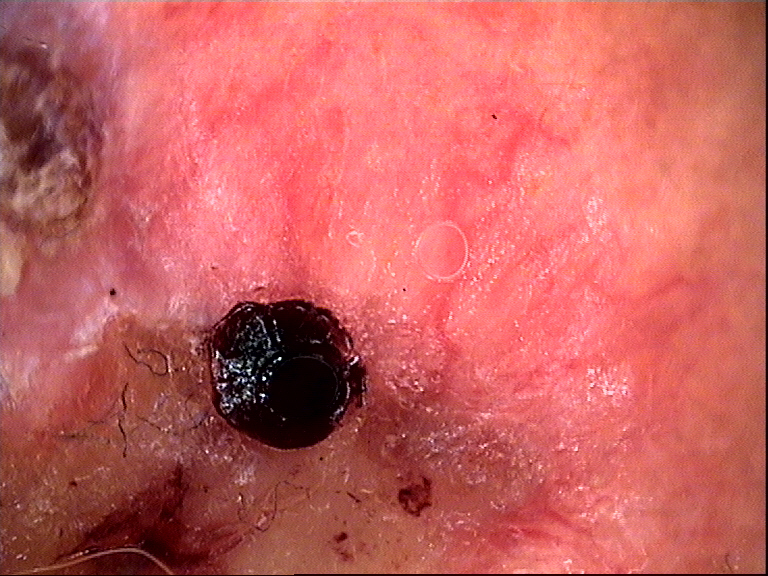Q: How is the lesion classified?
A: keratinocytic
Q: What is this lesion?
A: squamous cell carcinoma (biopsy-proven)